A dermoscopic close-up of a skin lesion, a female patient aged approximately 35 — 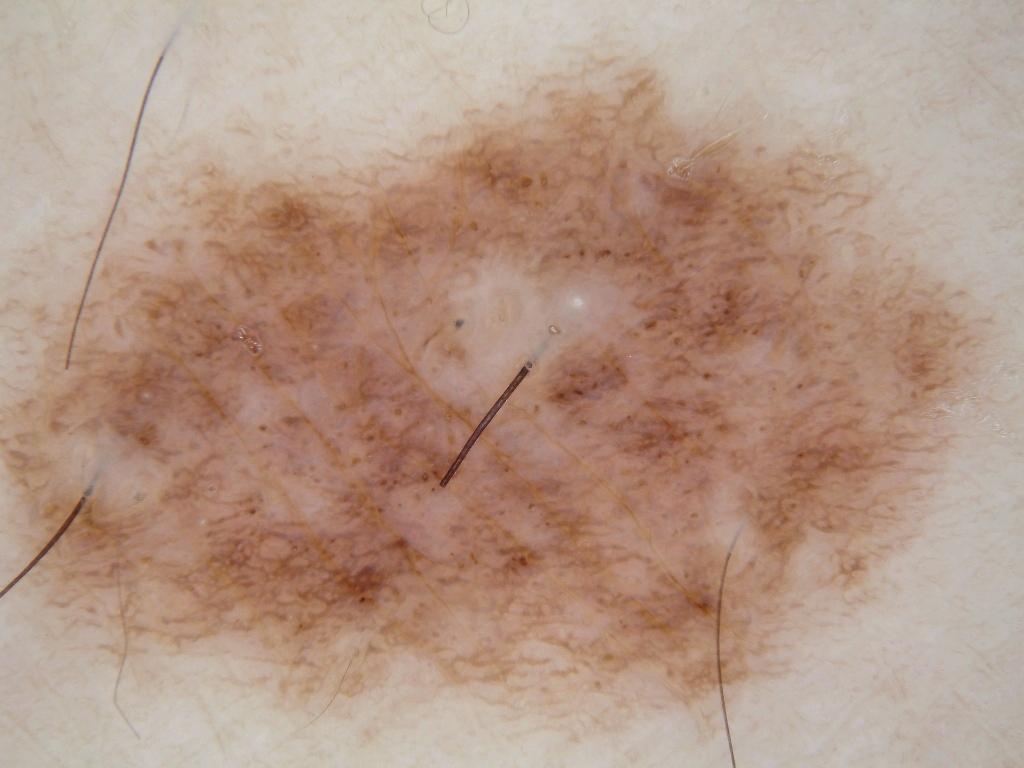On dermoscopy, the lesion shows pigment network and milia-like cysts; no globules, negative network, or streaks.
The lesion spans essentially the entire dermoscopic field.
Diagnosed as a melanocytic nevus.